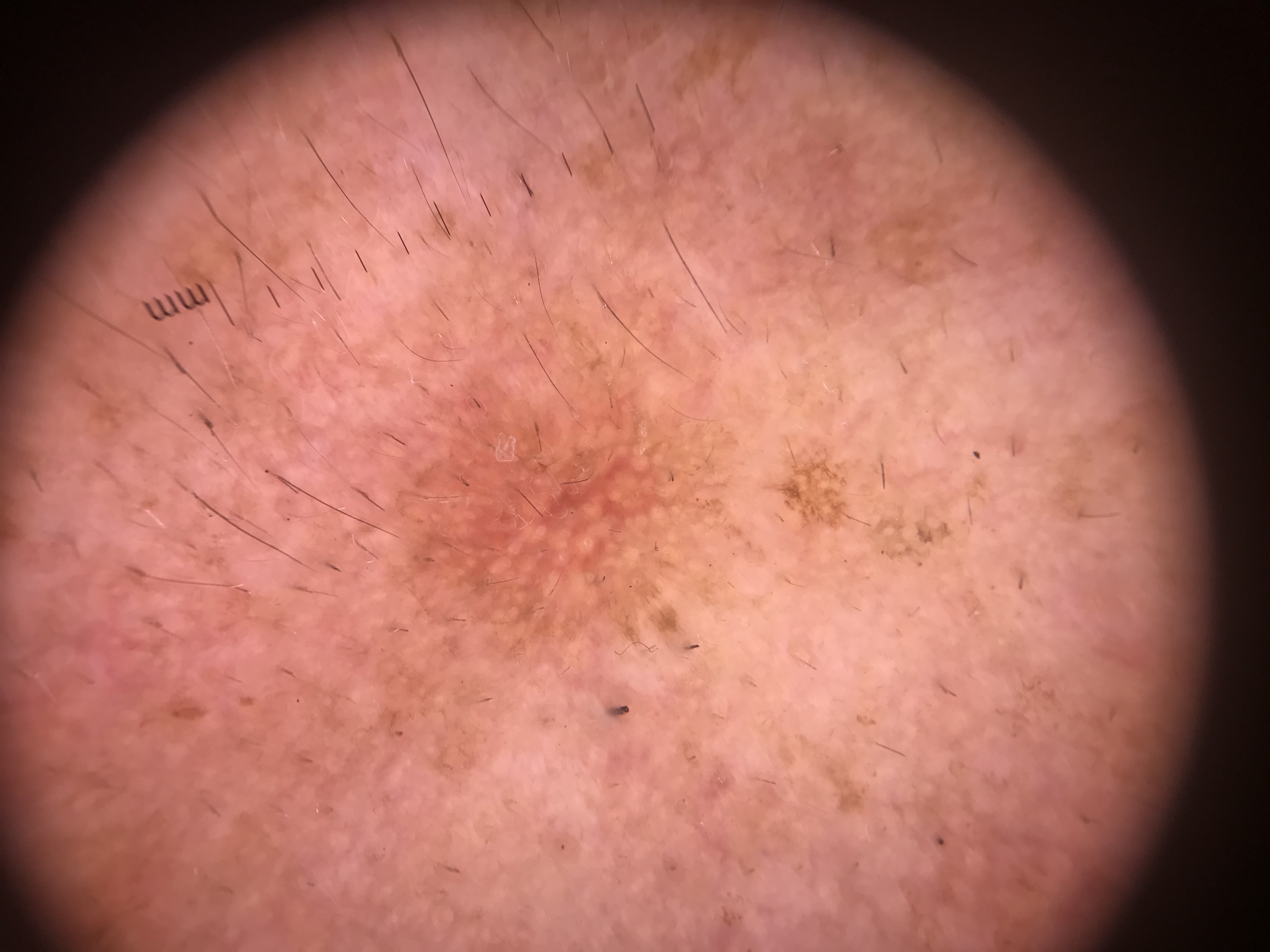Summary:
A dermatoscopic image of a skin lesion. The architecture is that of a keratinocytic lesion.
Conclusion:
Consistent with a lesion with uncertain malignant potential — an actinic keratosis.